An image taken at a distance.
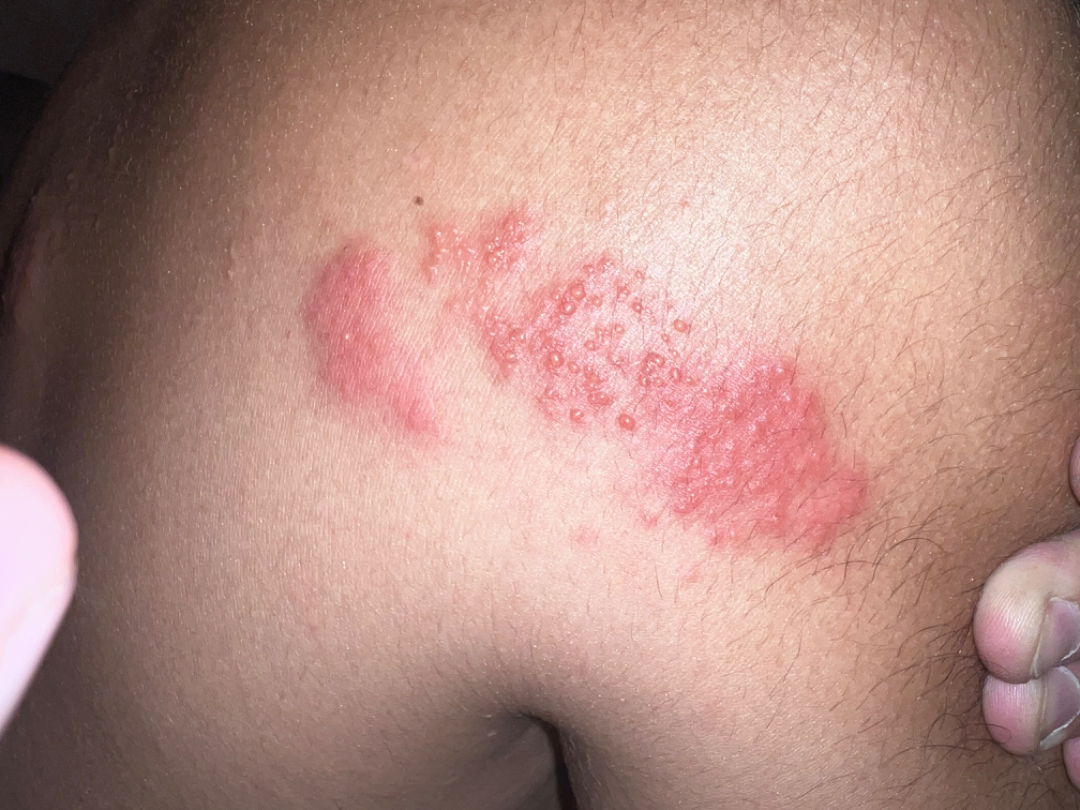{"differential": {"leading": ["Herpes Zoster"], "considered": ["Allergic Contact Dermatitis"]}}